The leg is involved · a close-up photograph: 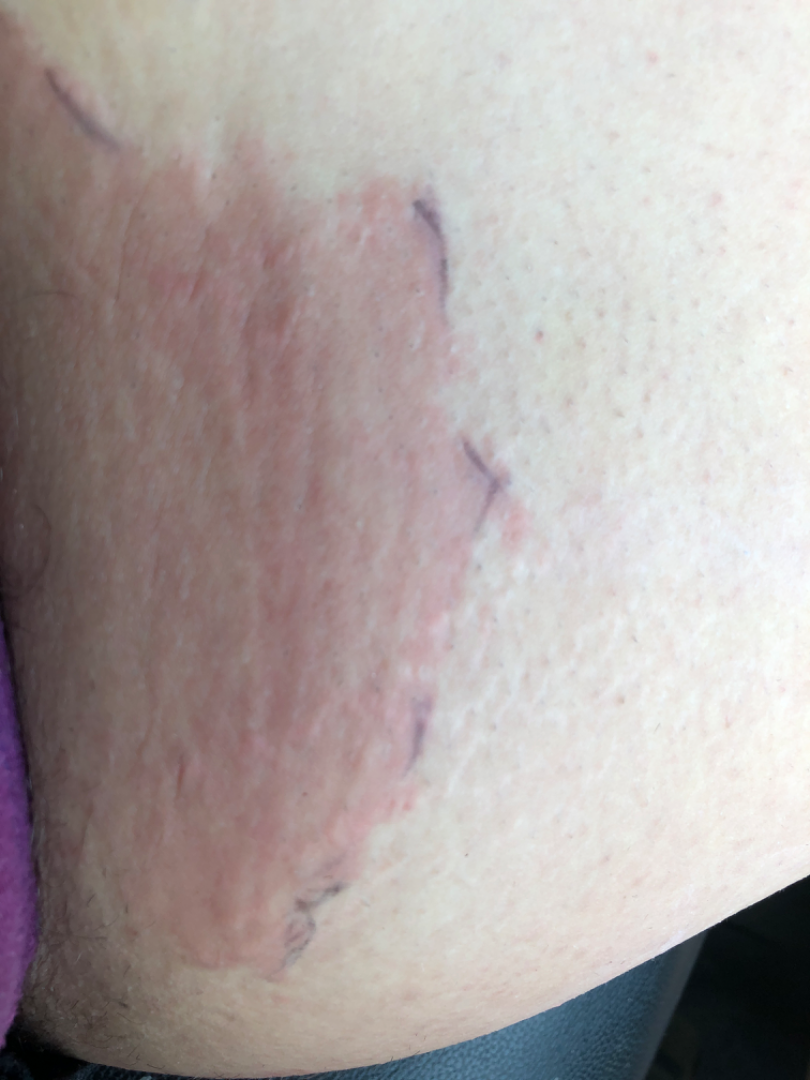One reviewing dermatologist: Cellulitis, Intertrigo and Psoriasis were considered with similar weight.